The patient is FST II; a clinical photo of a skin lesion taken with a smartphone; a female subject 39 years old.
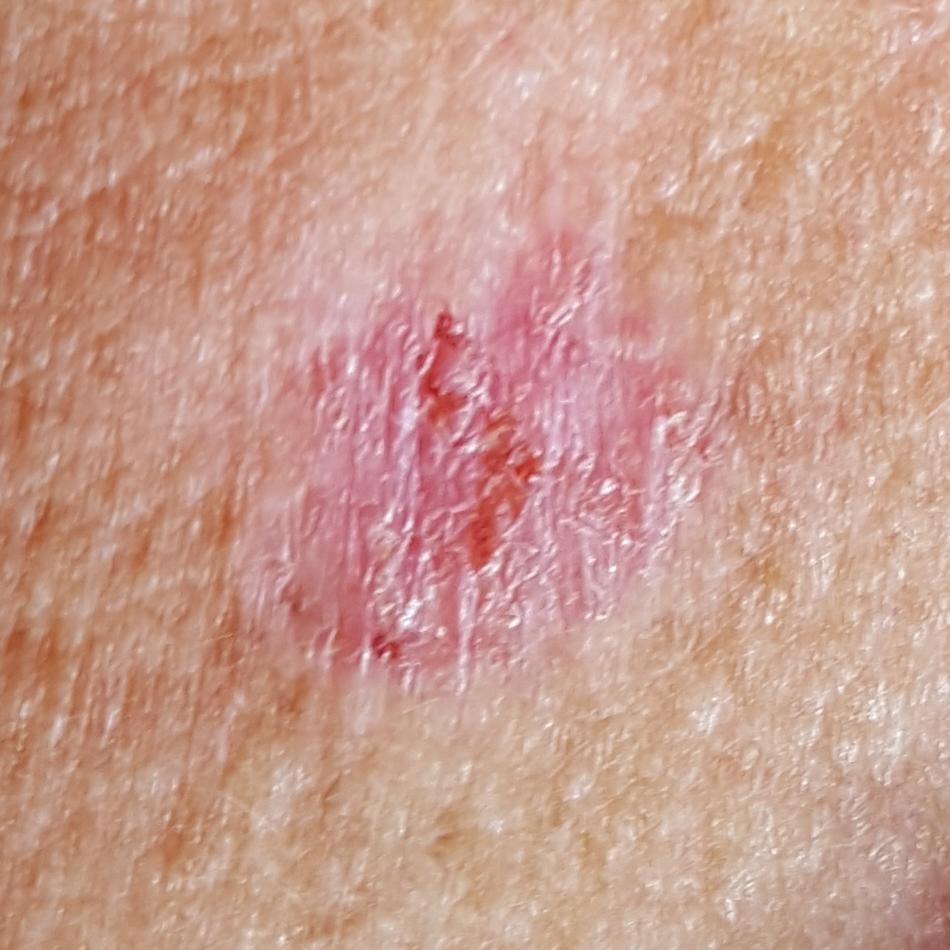Clinical context: The lesion was found on the neck. The lesion measures approximately 13 × 10 mm. Per patient report, the lesion itches, has grown, and has bled, but has not changed. Conclusion: Histopathology confirmed a basal cell carcinoma.